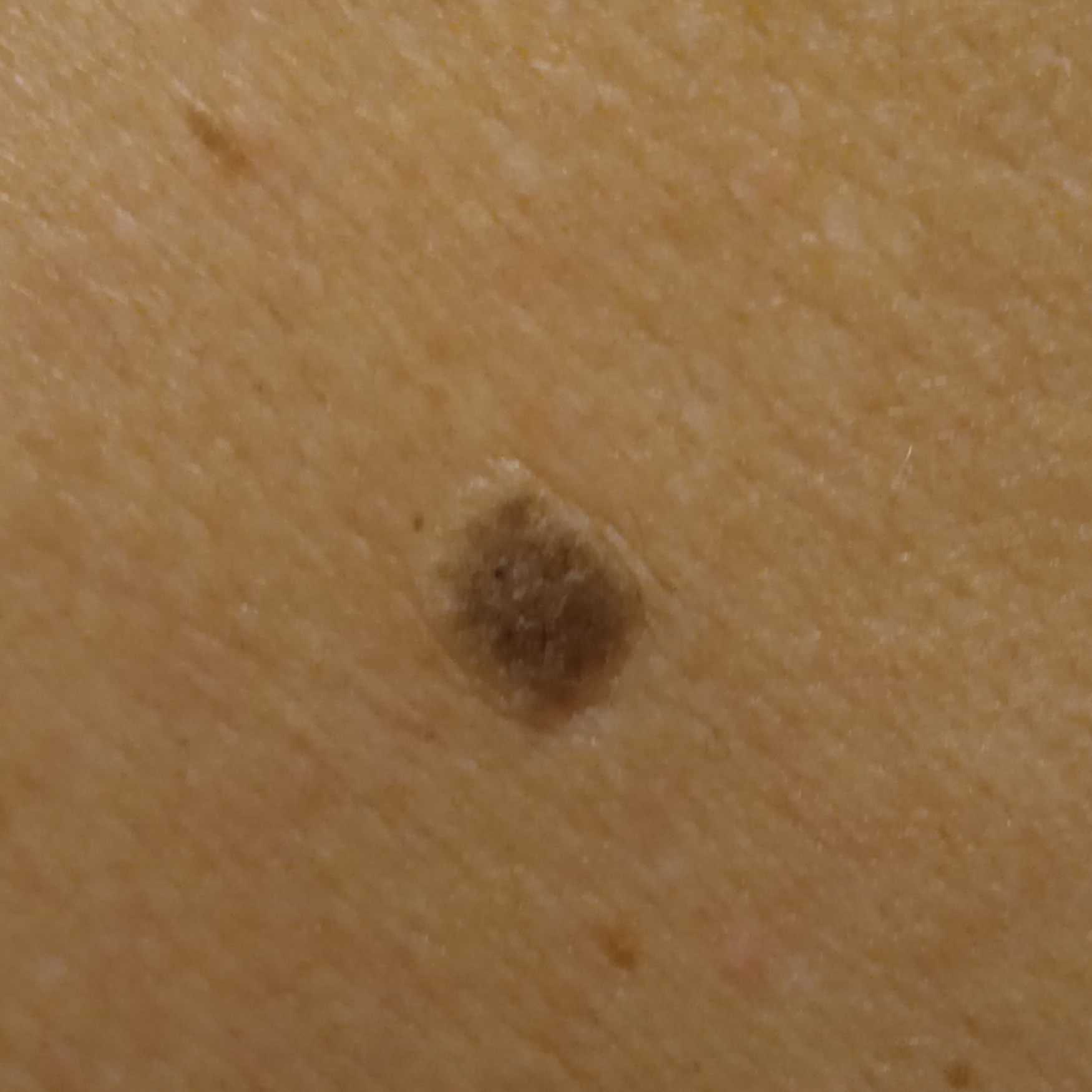Findings: Imaged for a research study, with no referral diagnosis recorded. A macroscopic clinical photograph of a skin lesion. A male patient age 67. Located on the back. Conclusion: The consensus diagnosis for this lesion was a seborrheic keratosis.